The chart records a prior melanoma but no first-degree relative with melanoma. A female patient about 65 years old. A dermatoscopic image of a skin lesion. Recorded as Fitzpatrick skin type III.
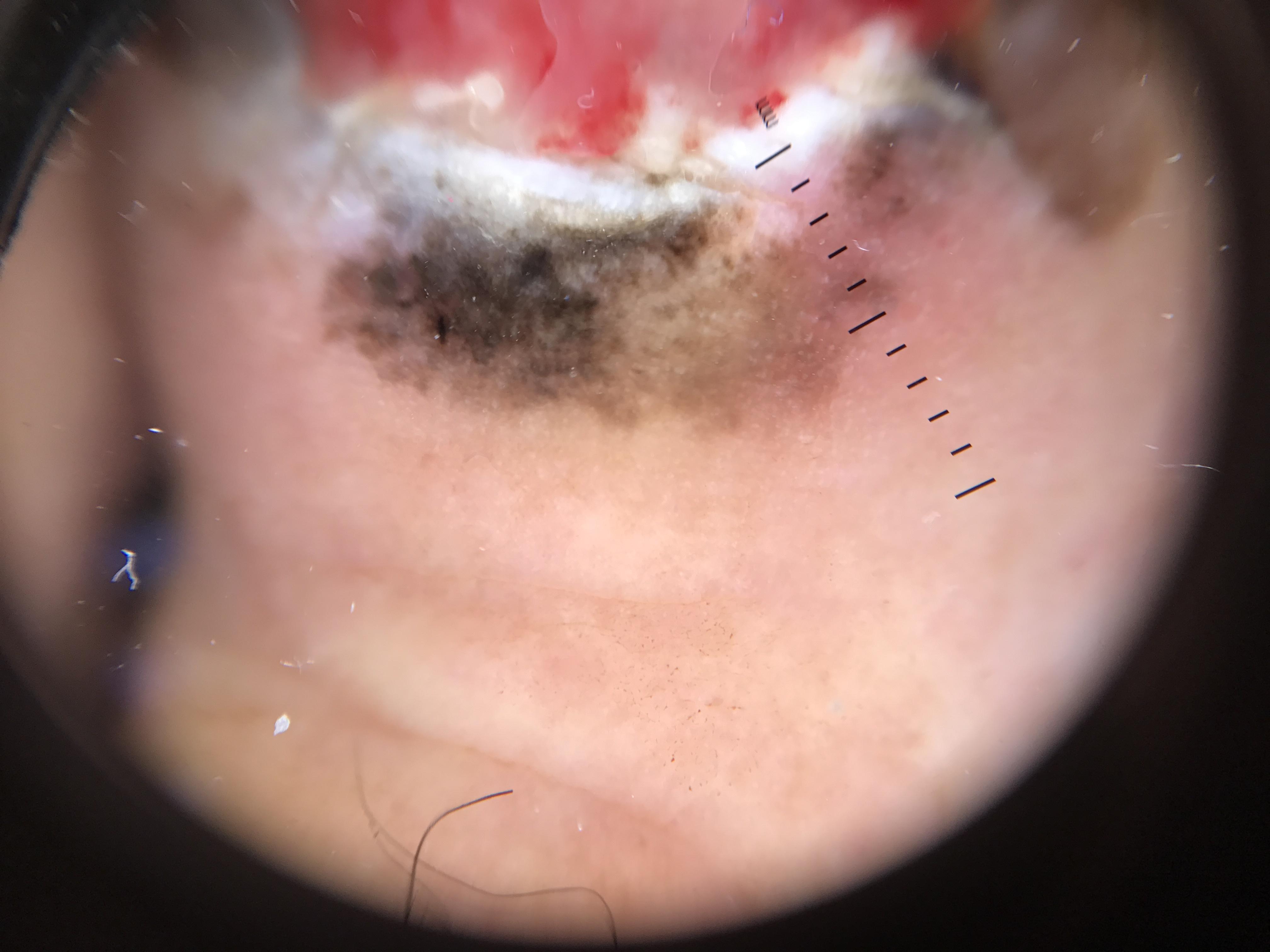The lesion involves a lower extremity. Histopathologically confirmed as a melanoma.